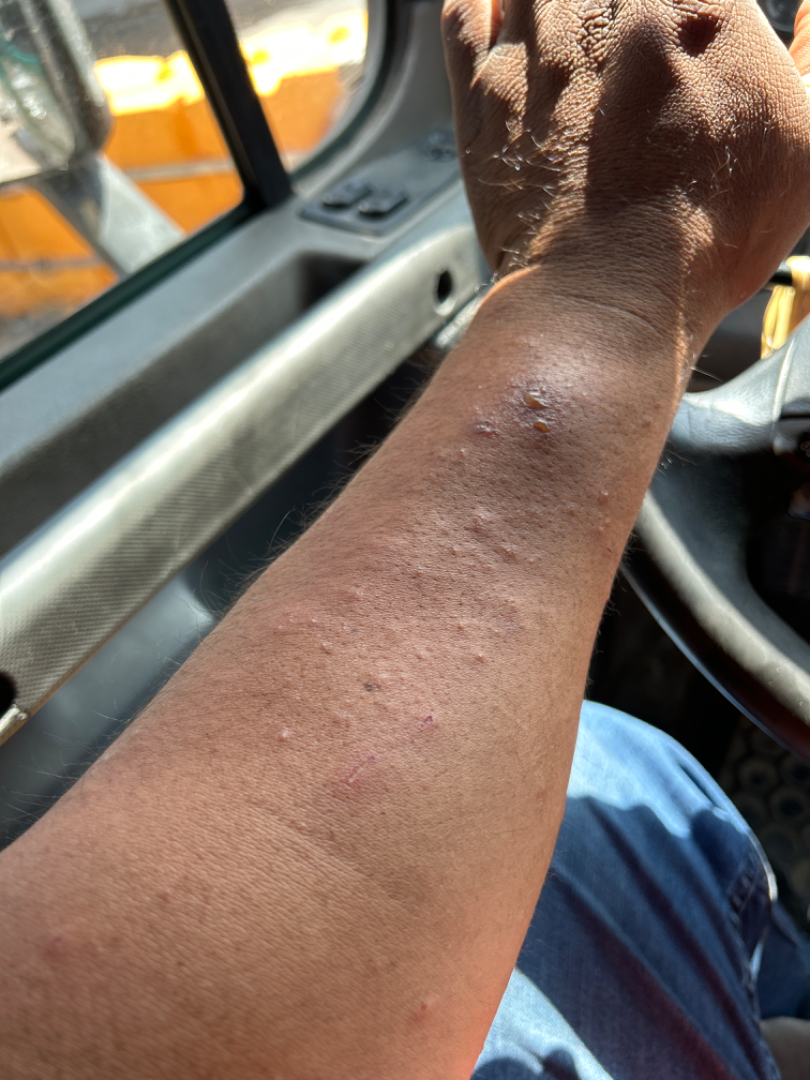The patient is 40–49, male.
The photograph is a close-up of the affected area.
Located on the arm.
Most likely Allergic Contact Dermatitis; lower on the differential is Acute dermatitis, NOS; less probable is Deep fungal infection; less likely is Abscess; a remote consideration is Eczema.